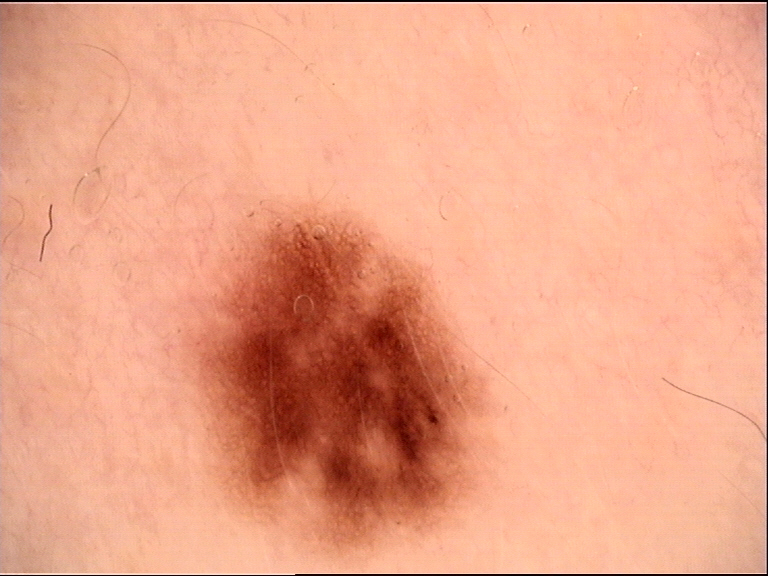diagnosis: dysplastic junctional nevus (expert consensus).